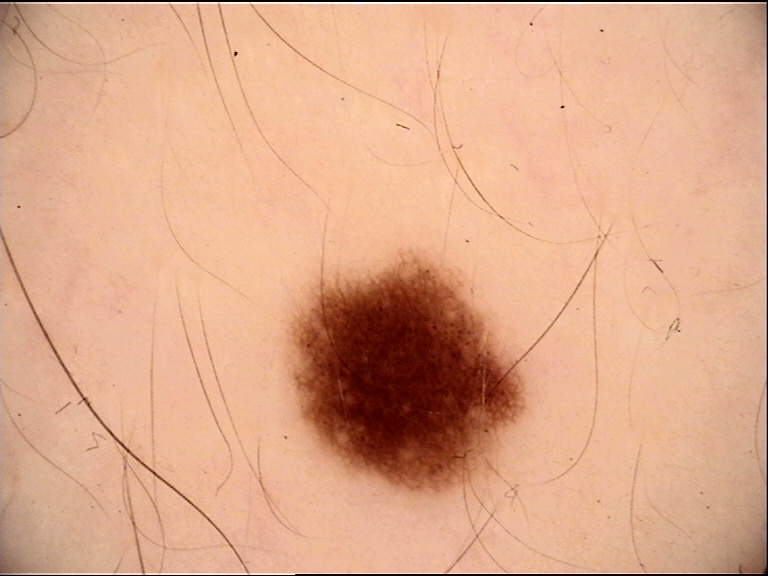Classified as a dysplastic junctional nevus.